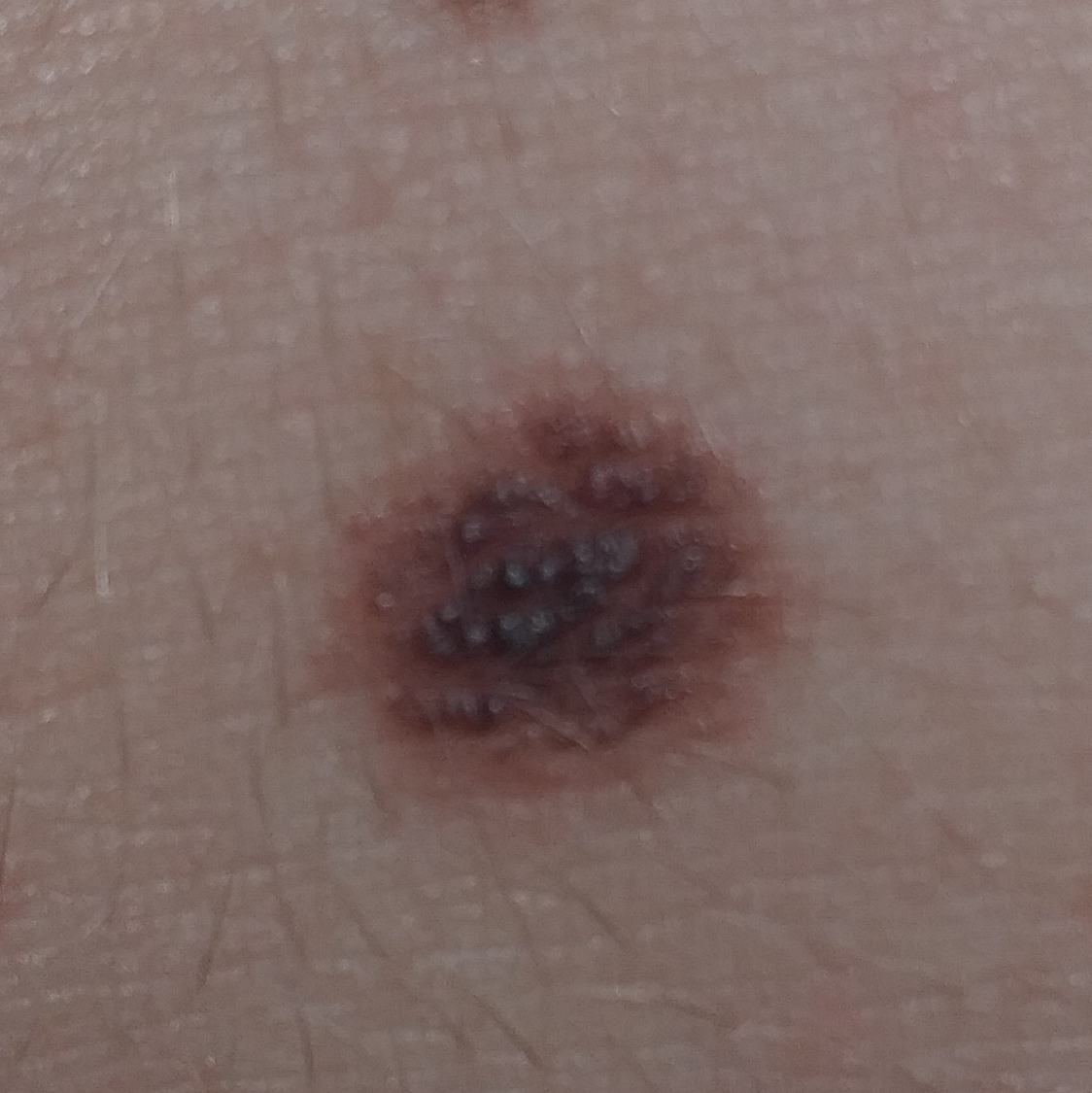The patient was assessed as Fitzpatrick phototype III.
A smartphone photograph of a skin lesion.
By history, prior malignancy (patient or family) and no pesticide exposure.
A female subject 27 years of age.
The lesion is located on the abdomen.
Measuring about 5 × 4 mm.
The patient describes that the lesion does not itch and has not bled.
Histopathological examination showed a nevus.